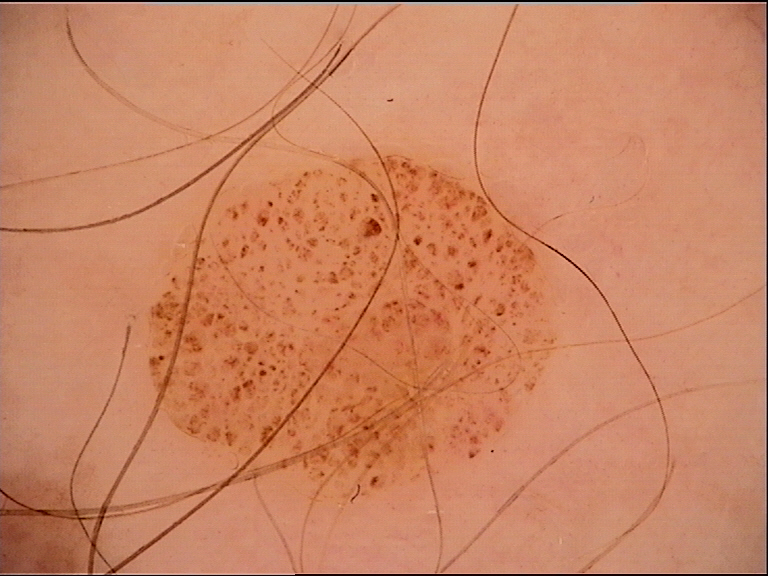• imaging: dermoscopy
• assessment: dysplastic junctional nevus (expert consensus)